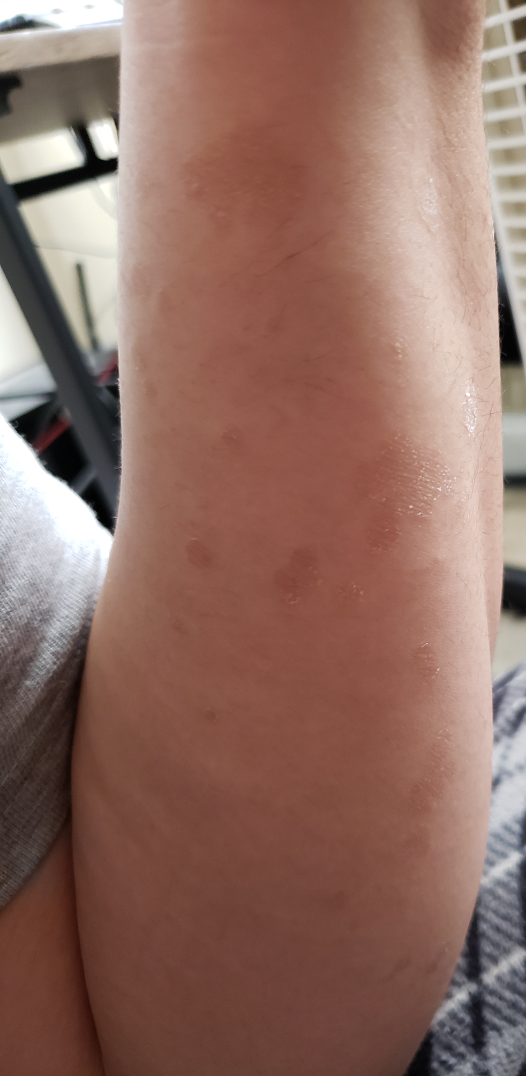On dermatologist assessment of the image, the differential is split between Psoriasis and Syphilis; also consider Tinea Versicolor; less probable is Pityriasis rosea.